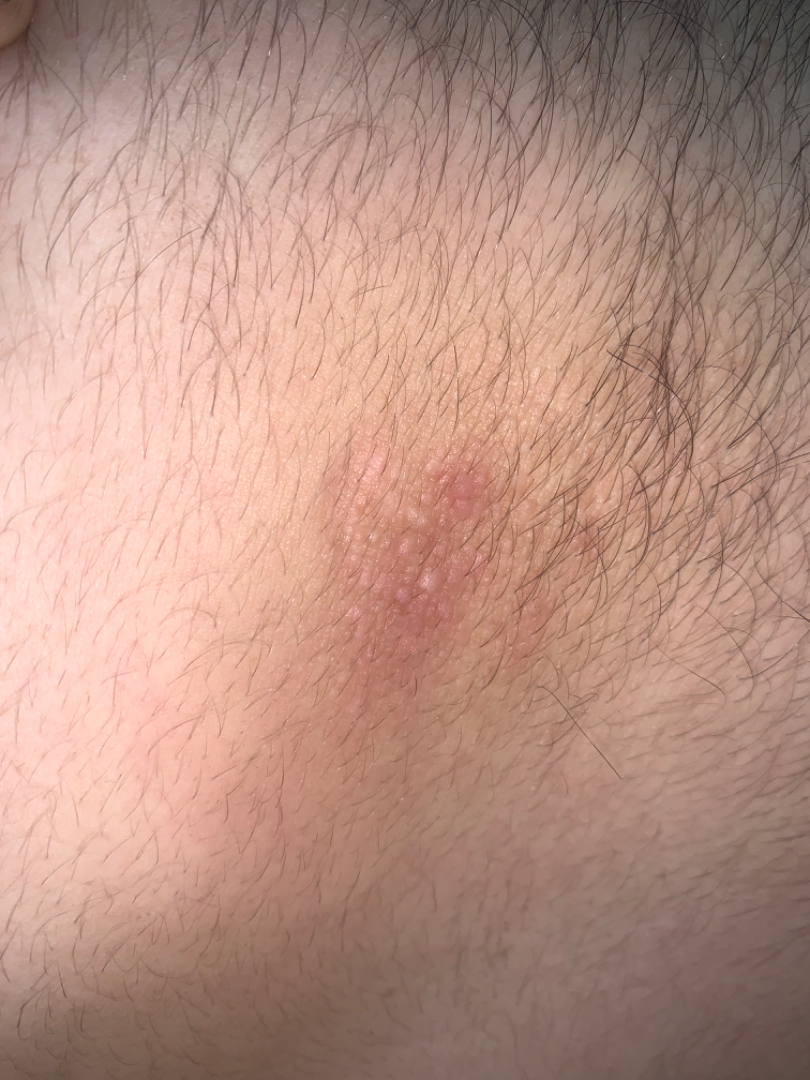Assessment:
No differential diagnosis could be assigned on photographic review.
Clinical context:
The patient reports the lesion is raised or bumpy. The patient reports associated fatigue. The patient reports the condition has been present for more than one year. The subject is a male aged 18–29. The photograph is a close-up of the affected area. Symptoms reported: bothersome appearance, darkening and itching. The patient described the issue as a rash.